The lesion is described as raised or bumpy and fluid-filled · the patient considered this a rash · the lesion is associated with bothersome appearance · the subject is a male aged 30–39 · the leg is involved · the patient also reports fatigue · close-up view · the contributor reports the condition has been present for three to twelve months:
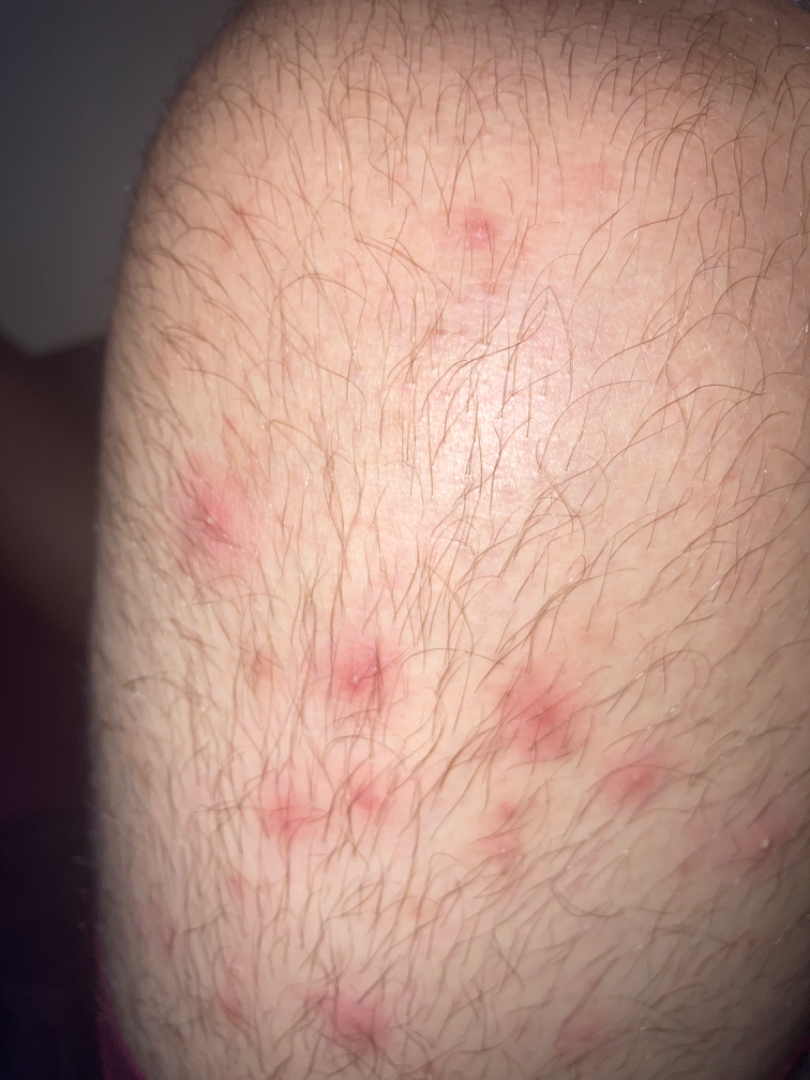Q: What is the differential diagnosis?
A: Folliculitis (weight 0.33); Insect Bite (weight 0.33); Skin and soft tissue atypical mycobacterial infection (weight 0.33)